The patient notes the condition has been present for one to three months. The lesion is associated with itching. The lesion is described as rough or flaky. Located on the leg. FST IV; non-clinician graders estimated Monk skin tone scale 4 (US pool) or 3 (India pool). The photo was captured at a distance: 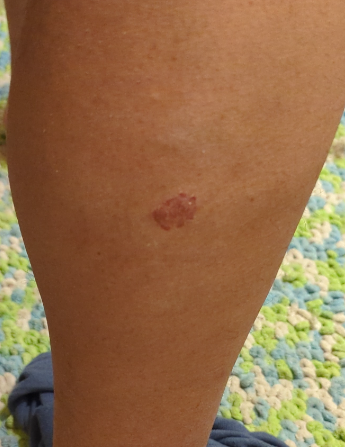<report>
<assessment>ungradable on photographic review</assessment>
</report>